The lesion involves the arm; the photo was captured at an angle: 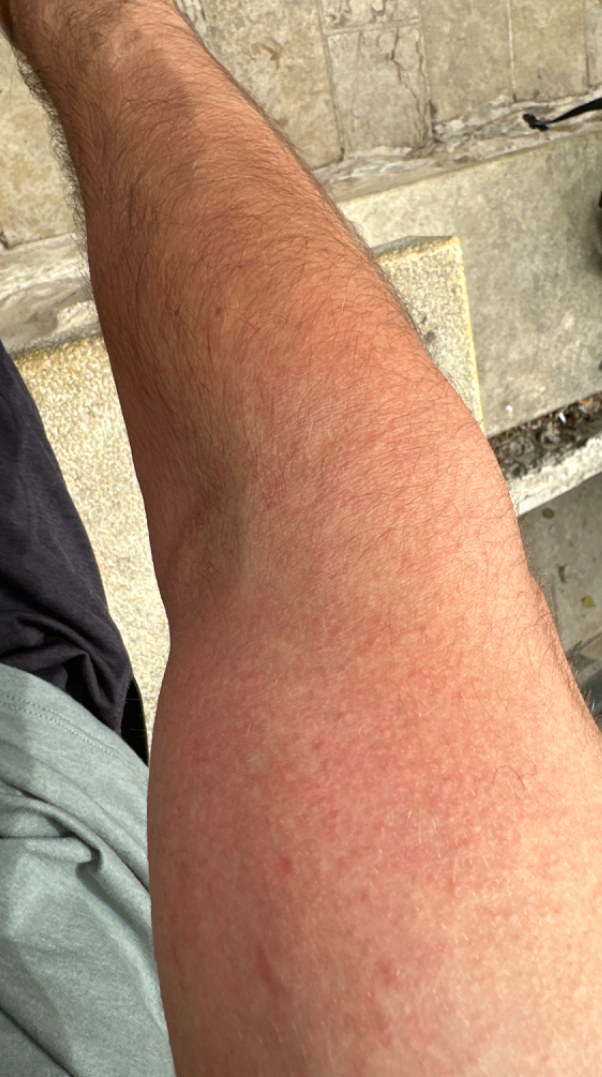present for: less than one week | symptoms: burning and itching | lesion texture: flat, rough or flaky and raised or bumpy | patient describes the issue as: a rash | assessment: Drug Rash (considered); Acute dermatitis, NOS (considered); Viral Exanthem (less likely); Allergic Contact Dermatitis (less likely); Eczema (less likely).